The subject is 18–29, female · a close-up photograph · located on the leg:
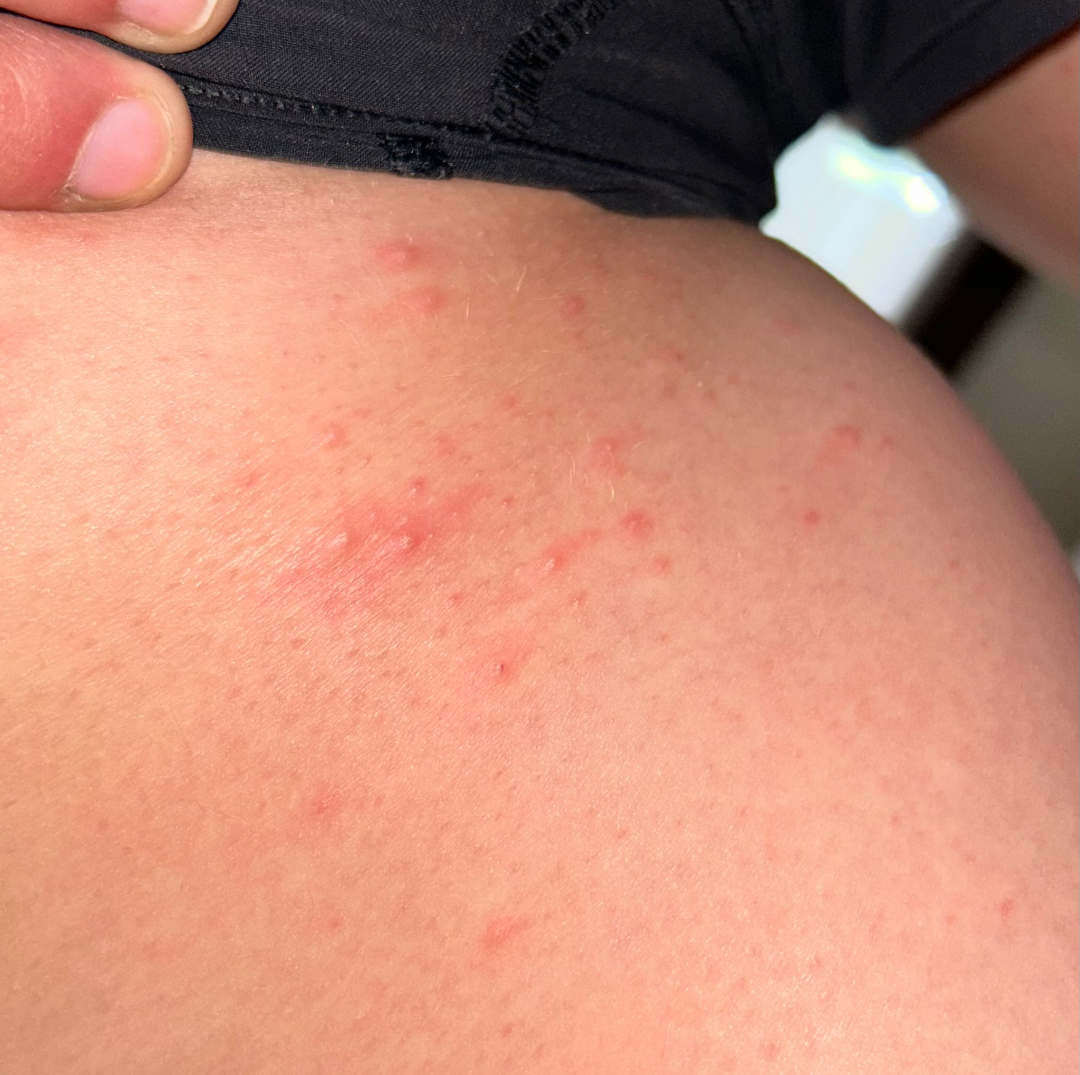The patient reports the lesion is raised or bumpy and fluid-filled. The patient reports the condition has been present for about one day. The lesion is associated with bothersome appearance. One reviewing dermatologist: in keeping with Folliculitis.